Located on the back of the torso · the contributor notes the lesion is flat and raised or bumpy · the patient considered this a rash · the photograph is a close-up of the affected area · skin tone: lay graders estimated 2 on the Monk skin tone scale · the lesion is associated with itching — 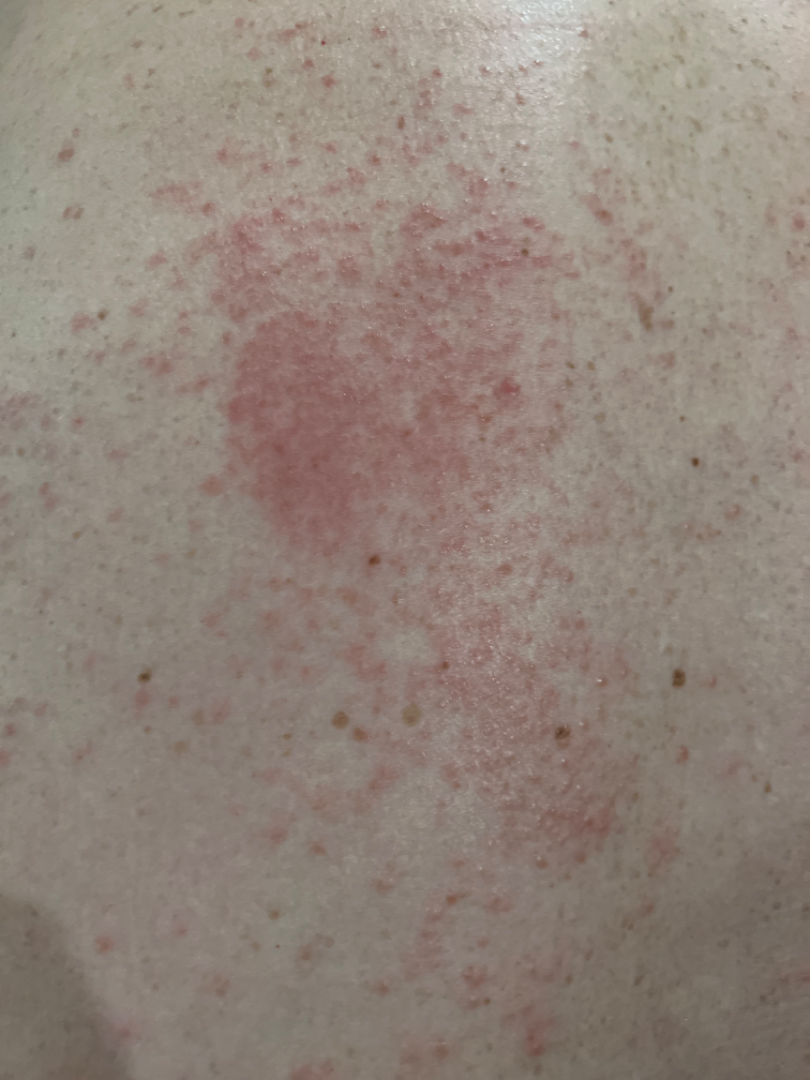<report>
  <differential>Acute dermatitis, NOS; Allergic Contact Dermatitis</differential>
</report>